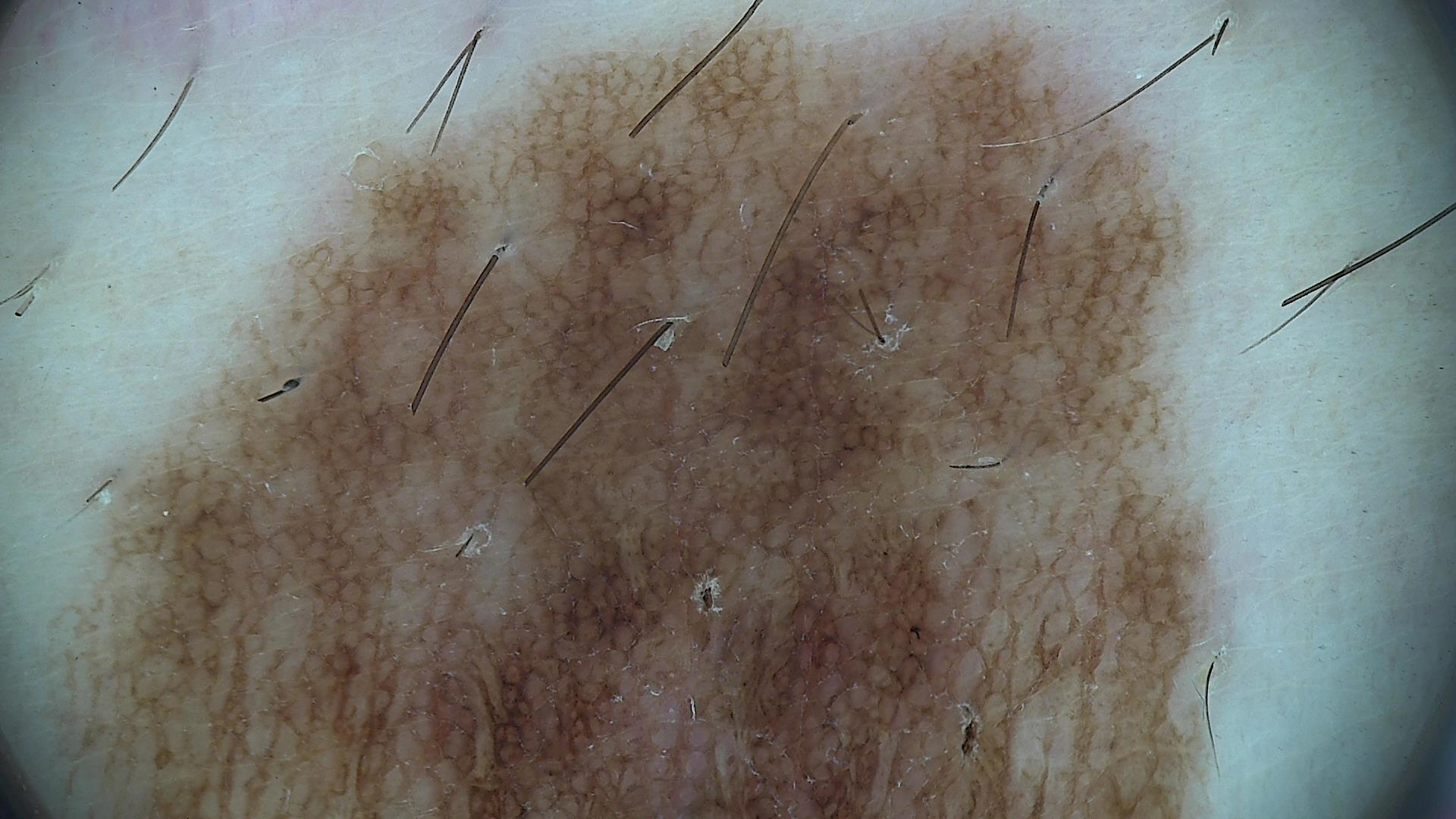Classified as a congenital dysplastic compound nevus.